Dermoscopy of a skin lesion: 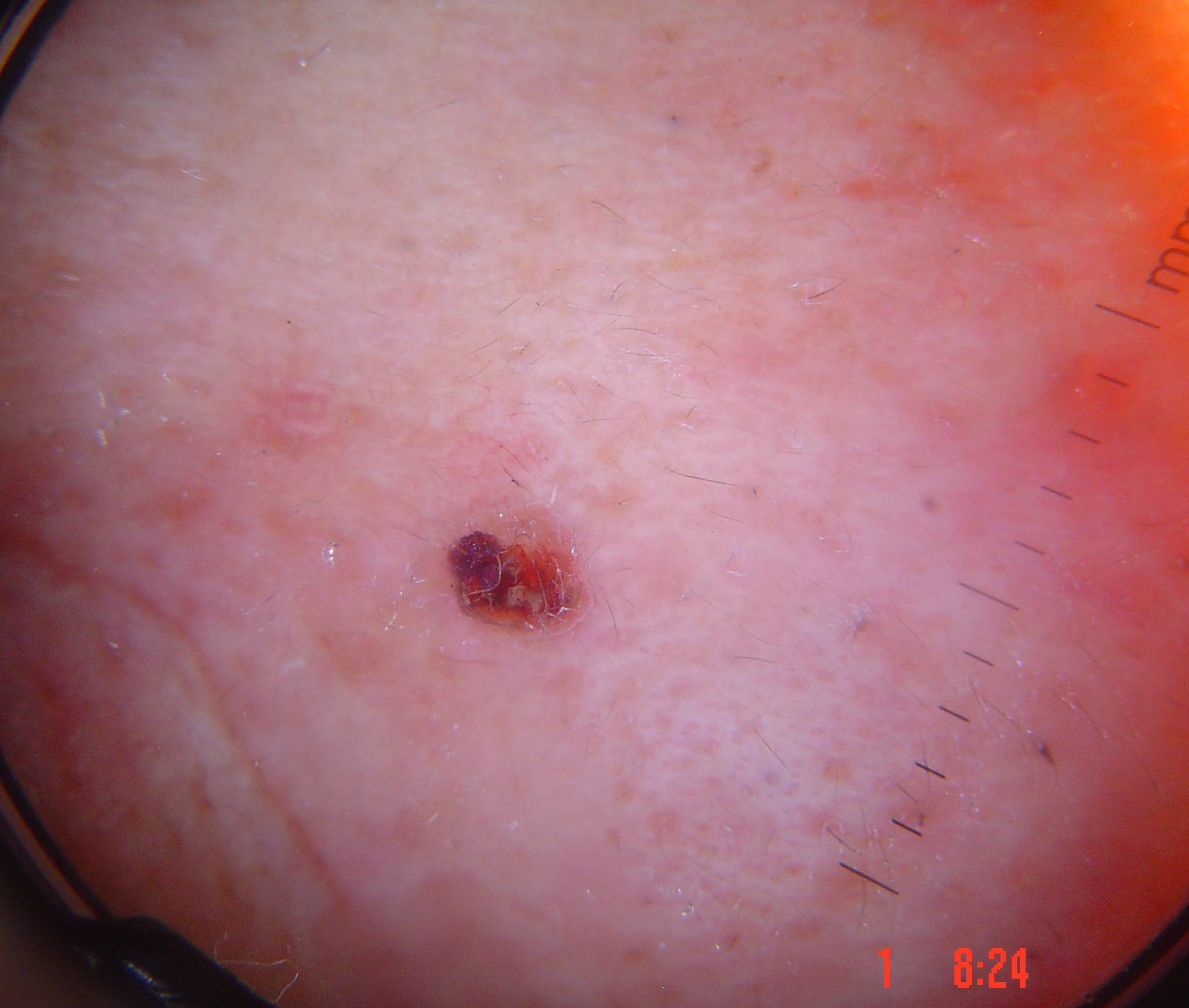Findings:
- lesion type — keratinocytic
- label — squamous cell carcinoma (biopsy-proven)